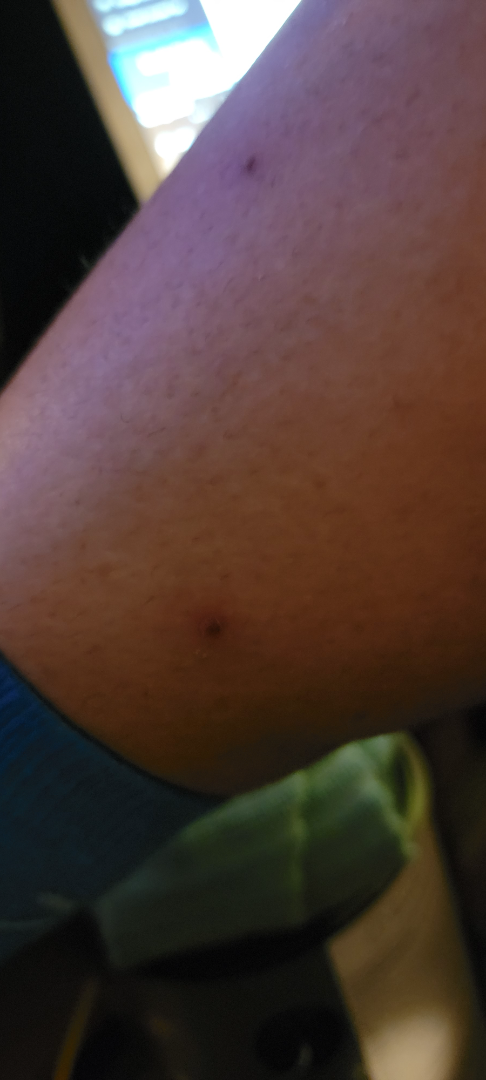Q: What was the assessment?
A: could not be assessed
Q: Image view?
A: at a distance
Q: Where on the body?
A: top or side of the foot, back of the hand, leg and arm
Q: Patient demographics?
A: female, age 50–59